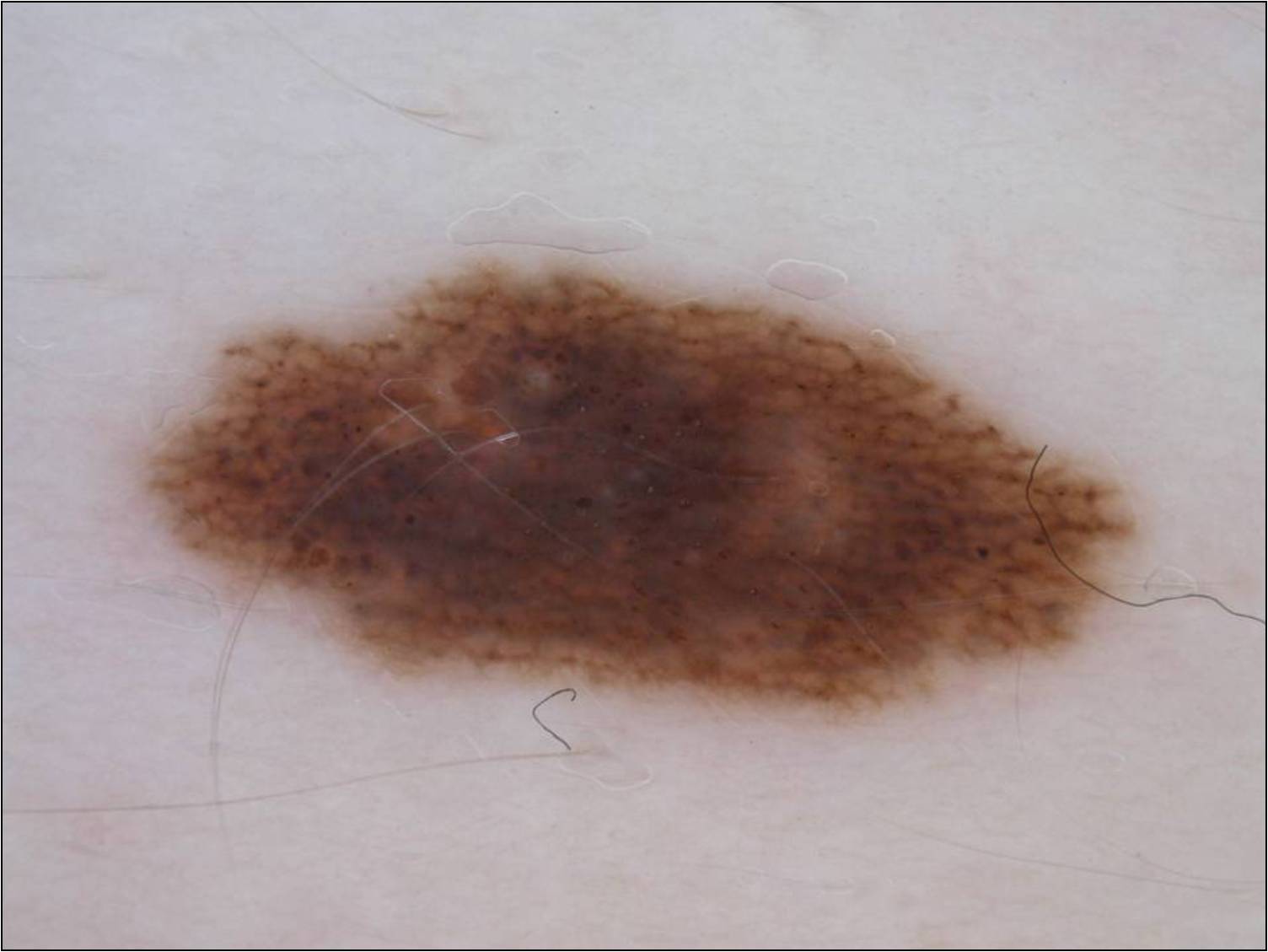A dermatoscopic image of a skin lesion. A female patient, roughly 30 years of age. Dermoscopy demonstrates globules and pigment network. With coordinates (x1, y1, x2, y2), the lesion's extent is box(144, 266, 1131, 713). Expert review diagnosed this as a melanocytic nevus, a benign lesion.